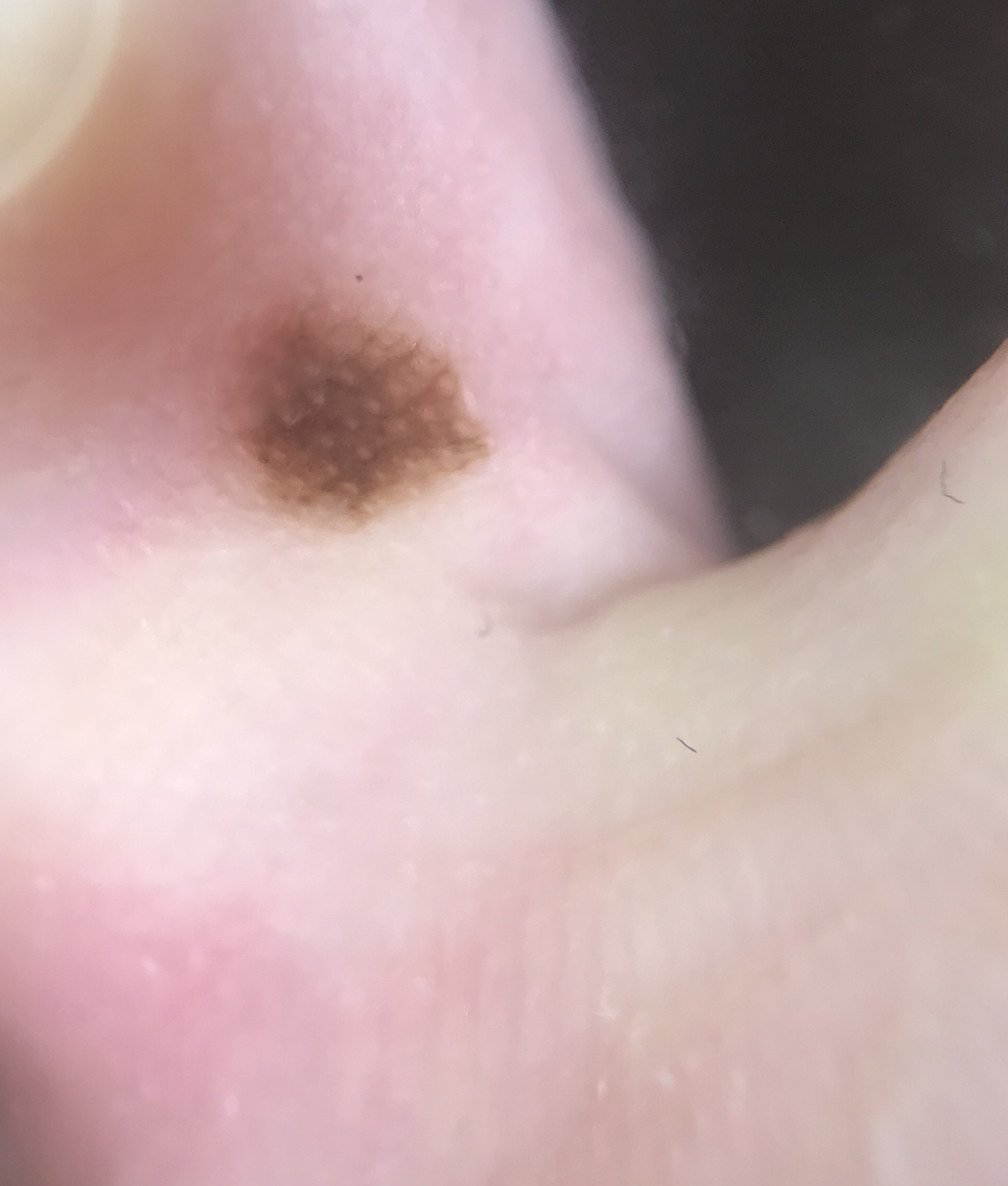A skin lesion imaged with a dermatoscope. This is a banal lesion. Labeled as an acral junctional nevus.